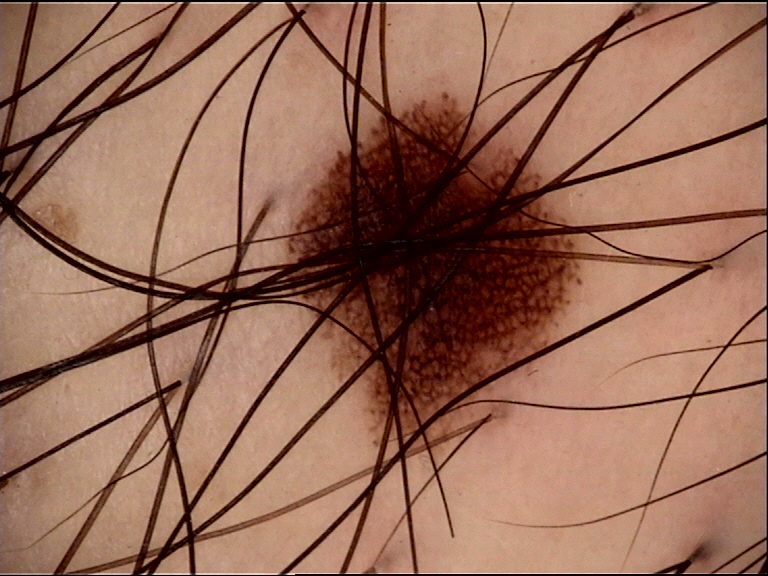Impression: Classified as a dysplastic junctional nevus.